A dermoscopic close-up of a skin lesion — 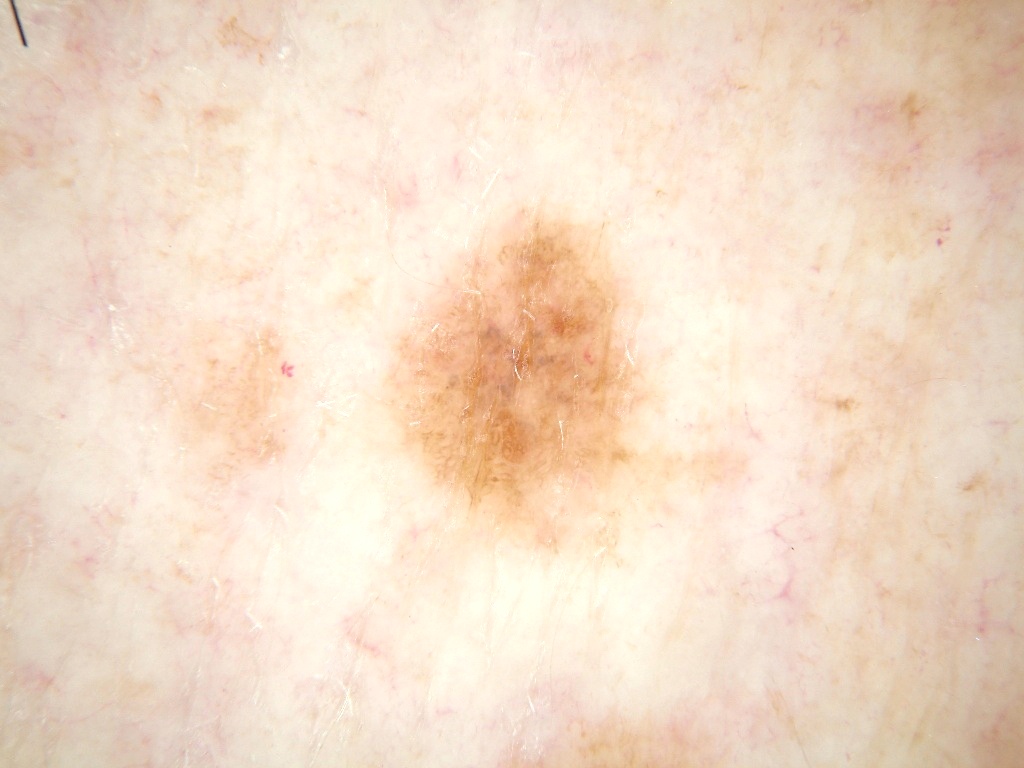<lesion>
  <lesion_location>
    <bbox_xyxy>377, 195, 764, 569</bbox_xyxy>
  </lesion_location>
  <diagnosis>
    <name>melanocytic nevus</name>
    <malignancy>benign</malignancy>
    <lineage>melanocytic</lineage>
    <provenance>clinical</provenance>
  </diagnosis>
</lesion>